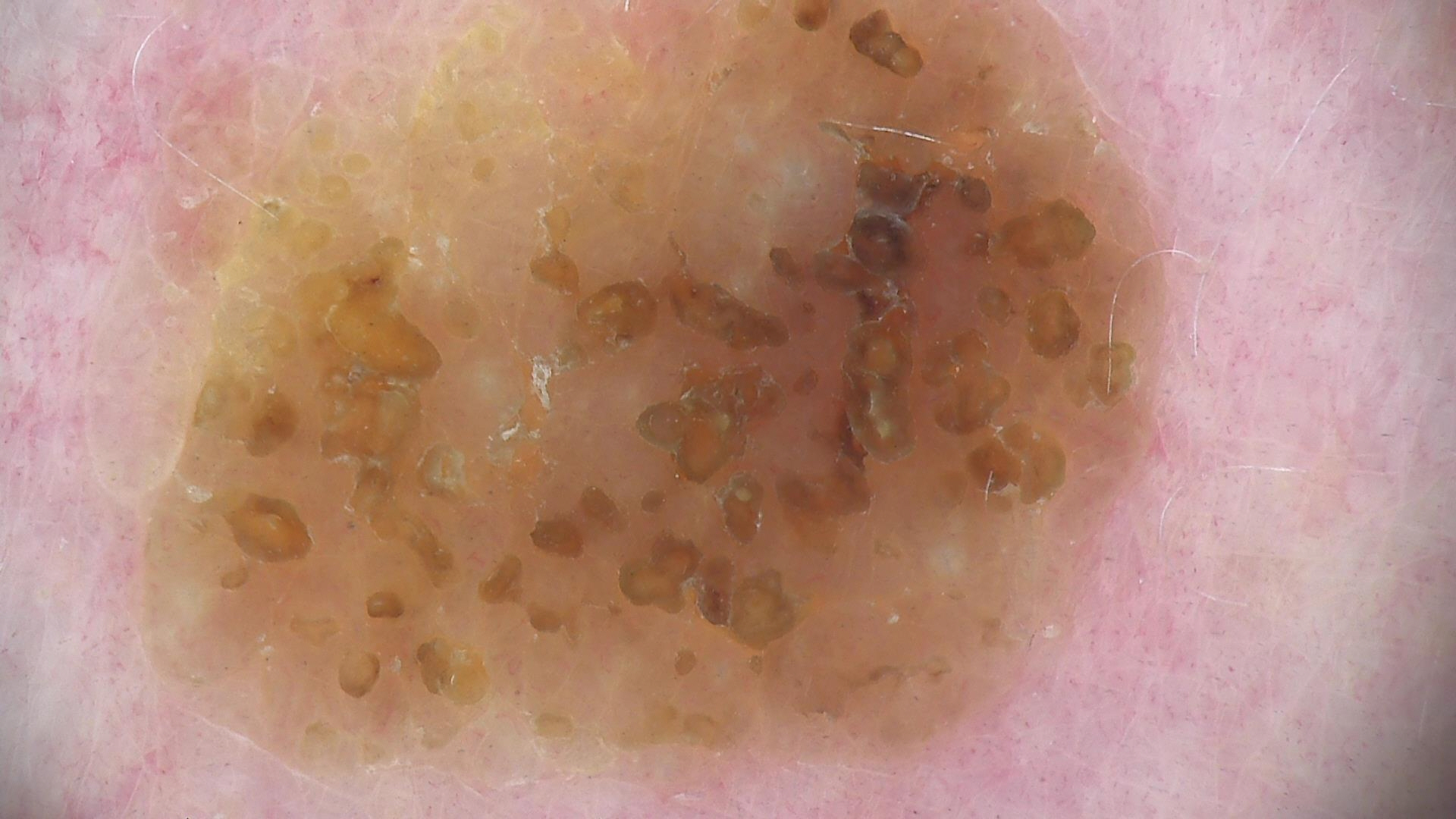class: seborrheic keratosis (expert consensus).